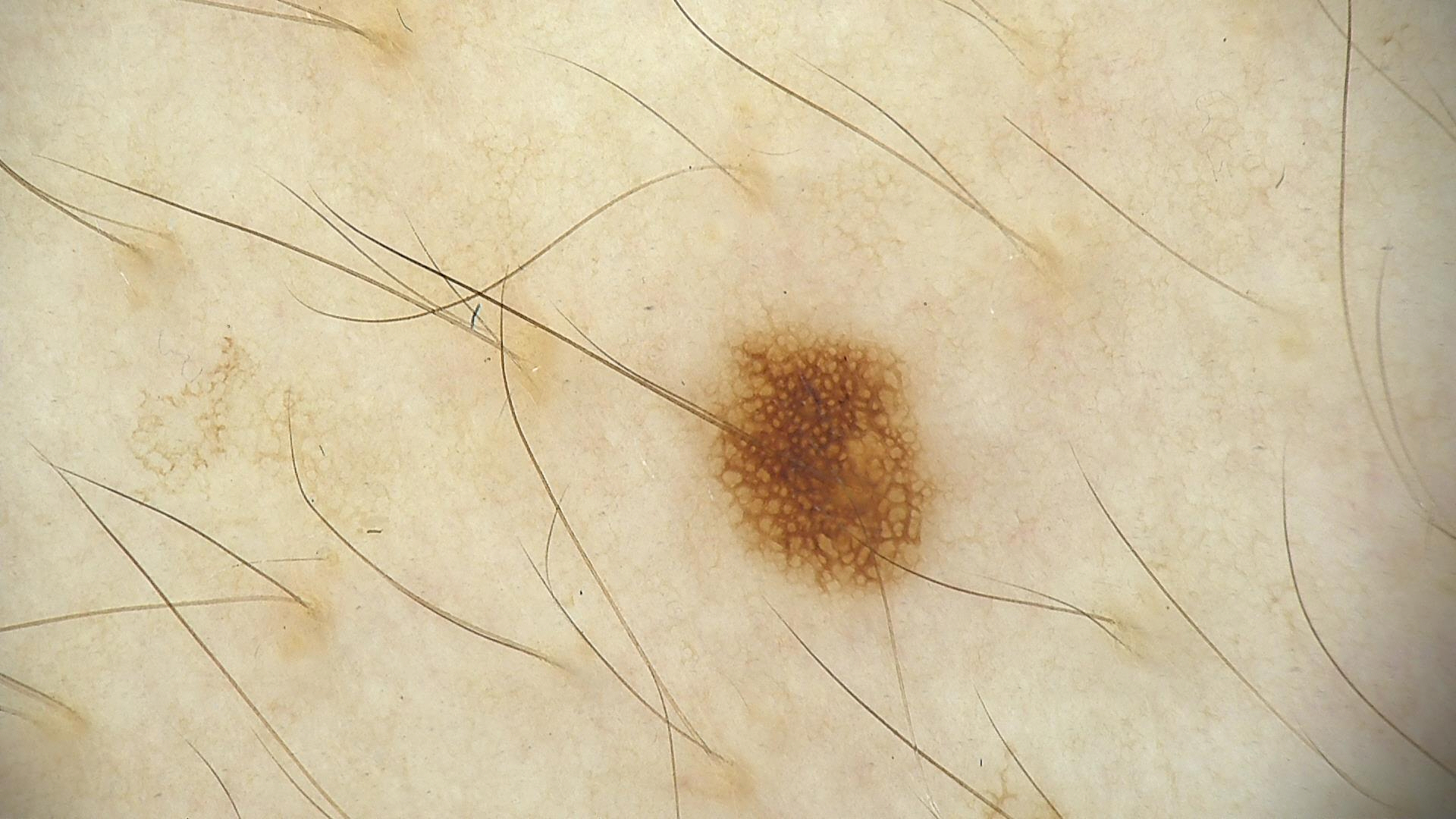image=dermatoscopy | assessment=dysplastic junctional nevus (expert consensus).